A male subject, in their mid- to late 40s; a dermoscopic image of a skin lesion — 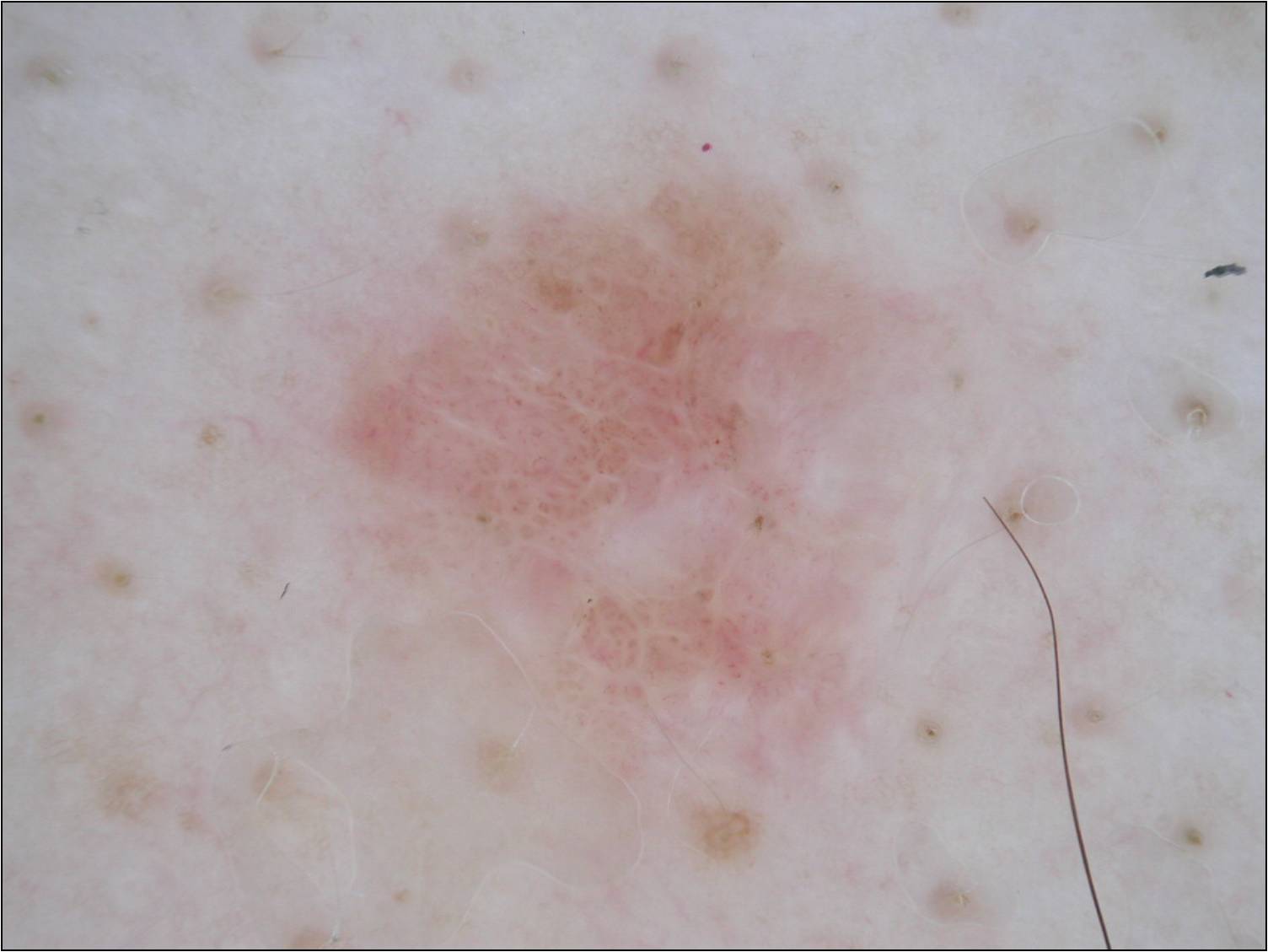Summary: Dermoscopically, the lesion shows negative network and globules. The lesion occupies the region bbox=[287, 112, 1070, 871]. The lesion covers approximately 33% of the dermoscopic field. Conclusion: Consistent with a melanocytic nevus.